Dermoscopy of a skin lesion, a male patient aged approximately 75 — 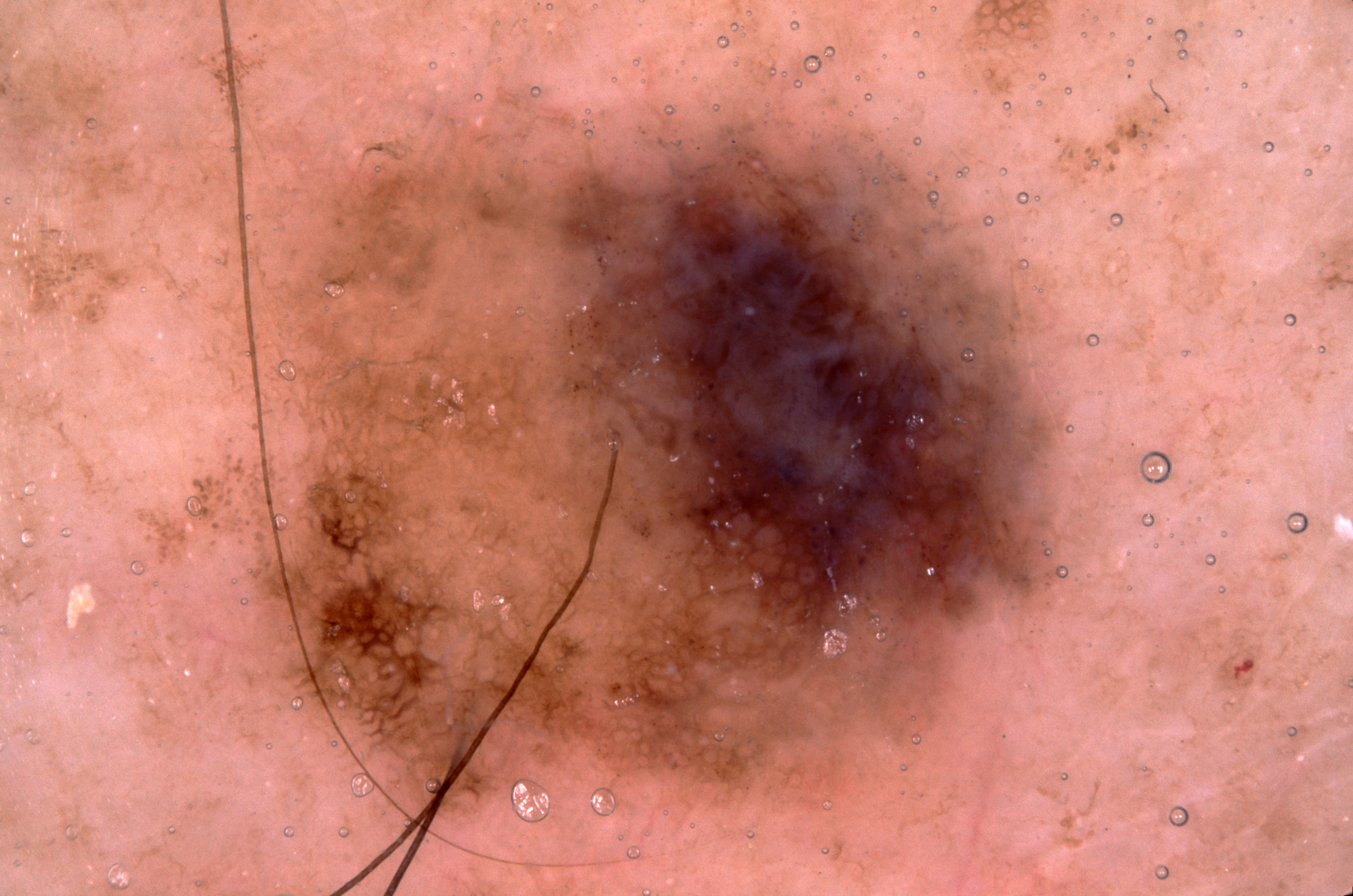Dermoscopic assessment notes pigment network.
The lesion takes up about 47% of the image.
The lesion spans x1=129, y1=64, x2=1090, y2=842.
On biopsy, the diagnosis was a melanoma.